A close-up photograph · the patient is 18–29, male · the back of the torso, arm and leg are involved.
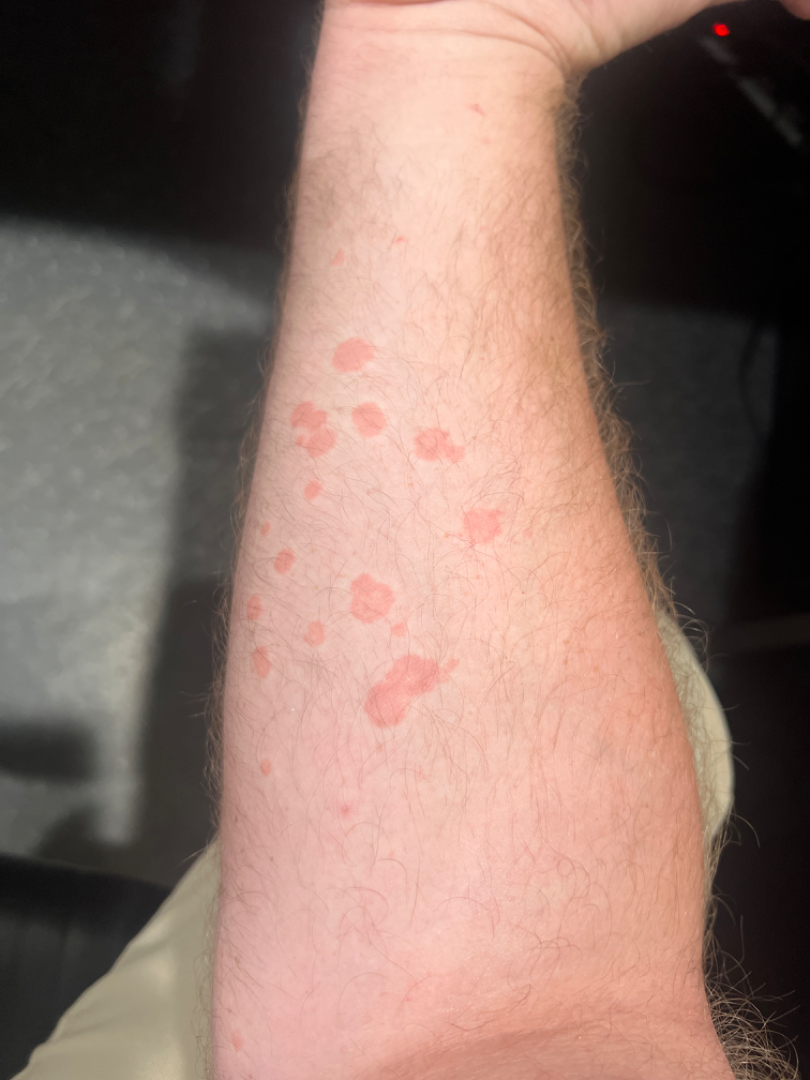Review: The condition could not be reliably identified from the image. Patient information: The patient described the issue as a rash. Texture is reported as flat. Reported lesion symptoms include bothersome appearance and enlargement.